A macroscopic clinical photograph of a skin lesion. The patient says their skin tans without first burning. A female patient aged 92. Acquired for a research image collection, with no referral diagnosis. The patient reports a personal history of cancer and a family history of skin cancer:
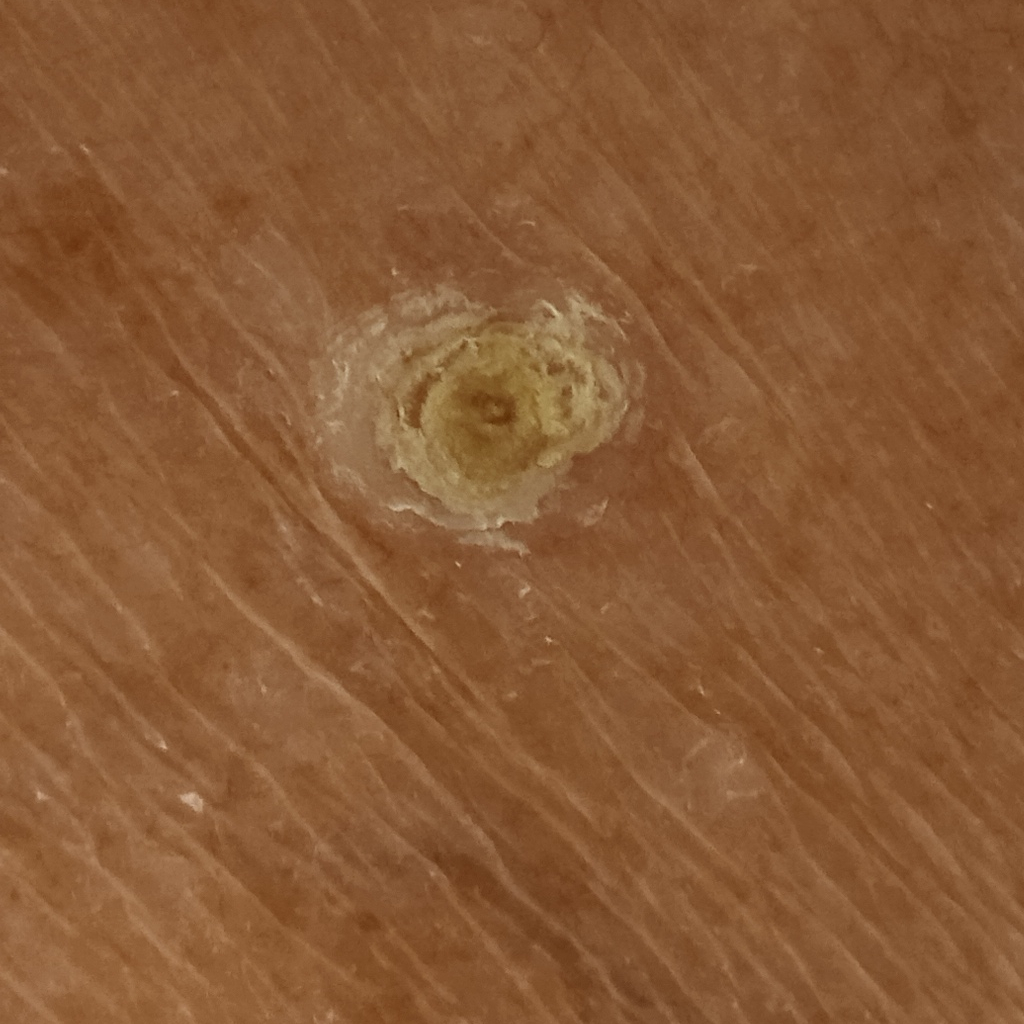The lesion involves the torso.
The lesion is about 12.5 mm across.
The dermatologists' assessment was a squamous cell carcinoma.